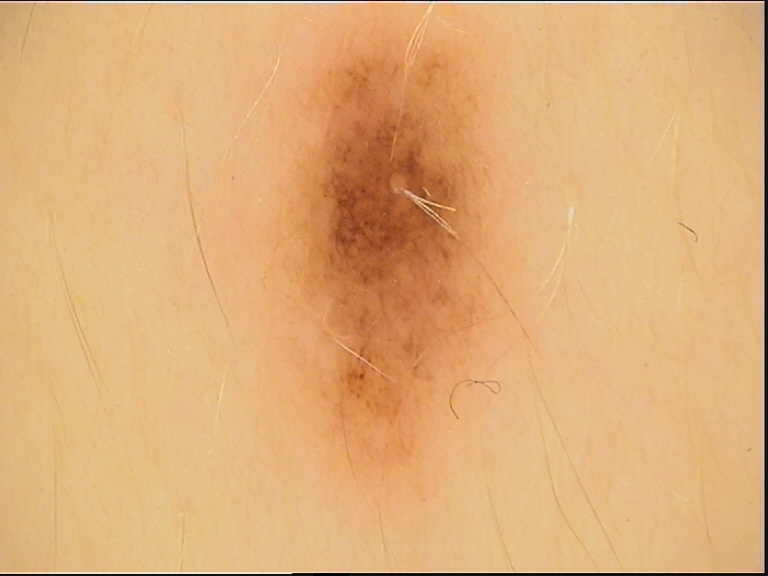Classified as a dysplastic junctional nevus.